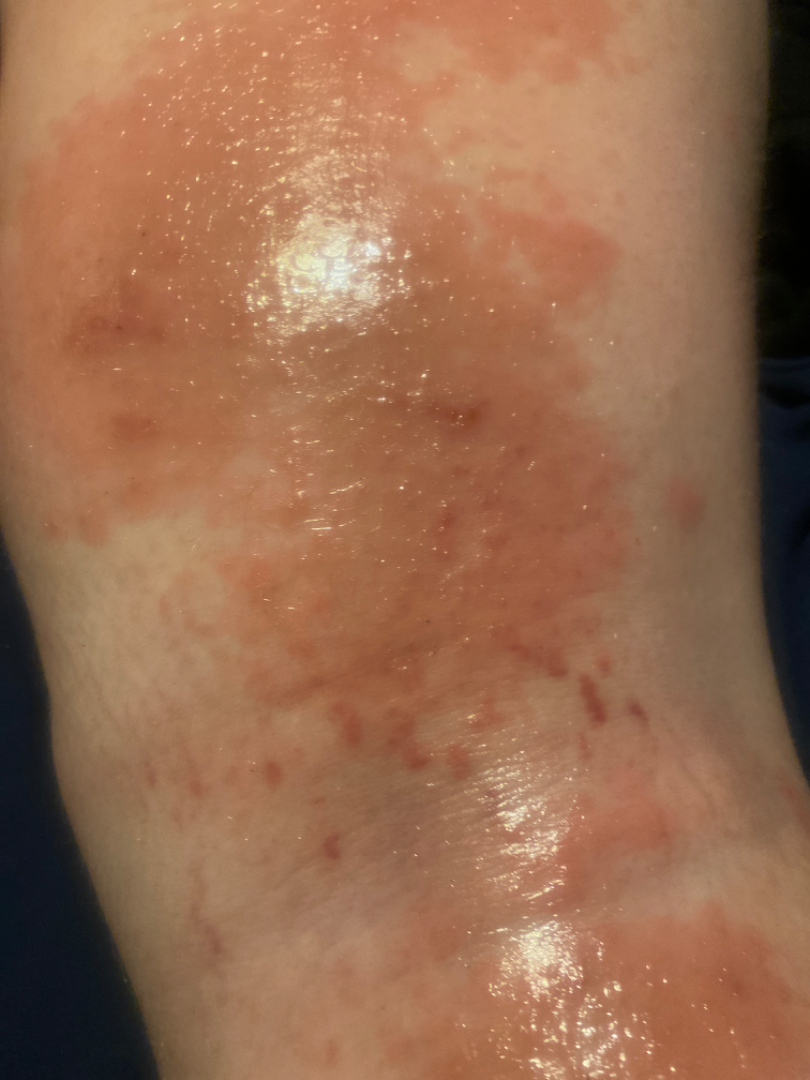The photograph is a close-up of the affected area.
The patient described the issue as a rash.
The leg is involved.
Present for less than one week.
Fitzpatrick phototype II.
The subject is 30–39, female.
The contributor notes itching.
On remote dermatologist review, Allergic Contact Dermatitis (leading); Eczema (possible); Psoriasis (lower probability).